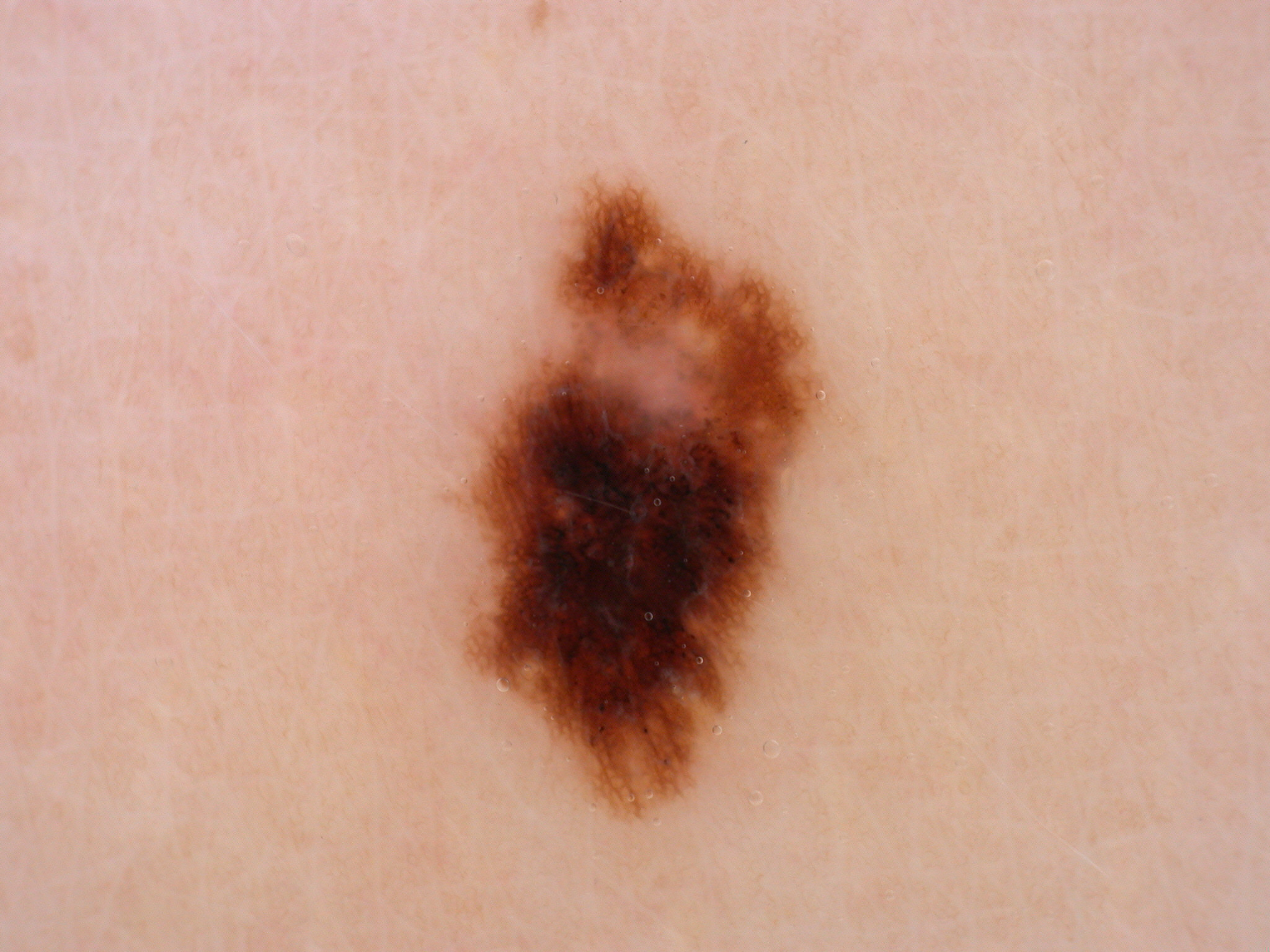  image:
    modality: dermoscopy
  lesion_location:
    bbox_xyxy:
      - 464
      - 188
      - 823
      - 820
  dermoscopic_features:
    present:
      - streaks
      - pigment network
      - globules
    absent:
      - negative network
      - milia-like cysts
  diagnosis:
    name: melanocytic nevus
    malignancy: benign
    lineage: melanocytic
    provenance: clinical